A dermoscopic image of a skin lesion.
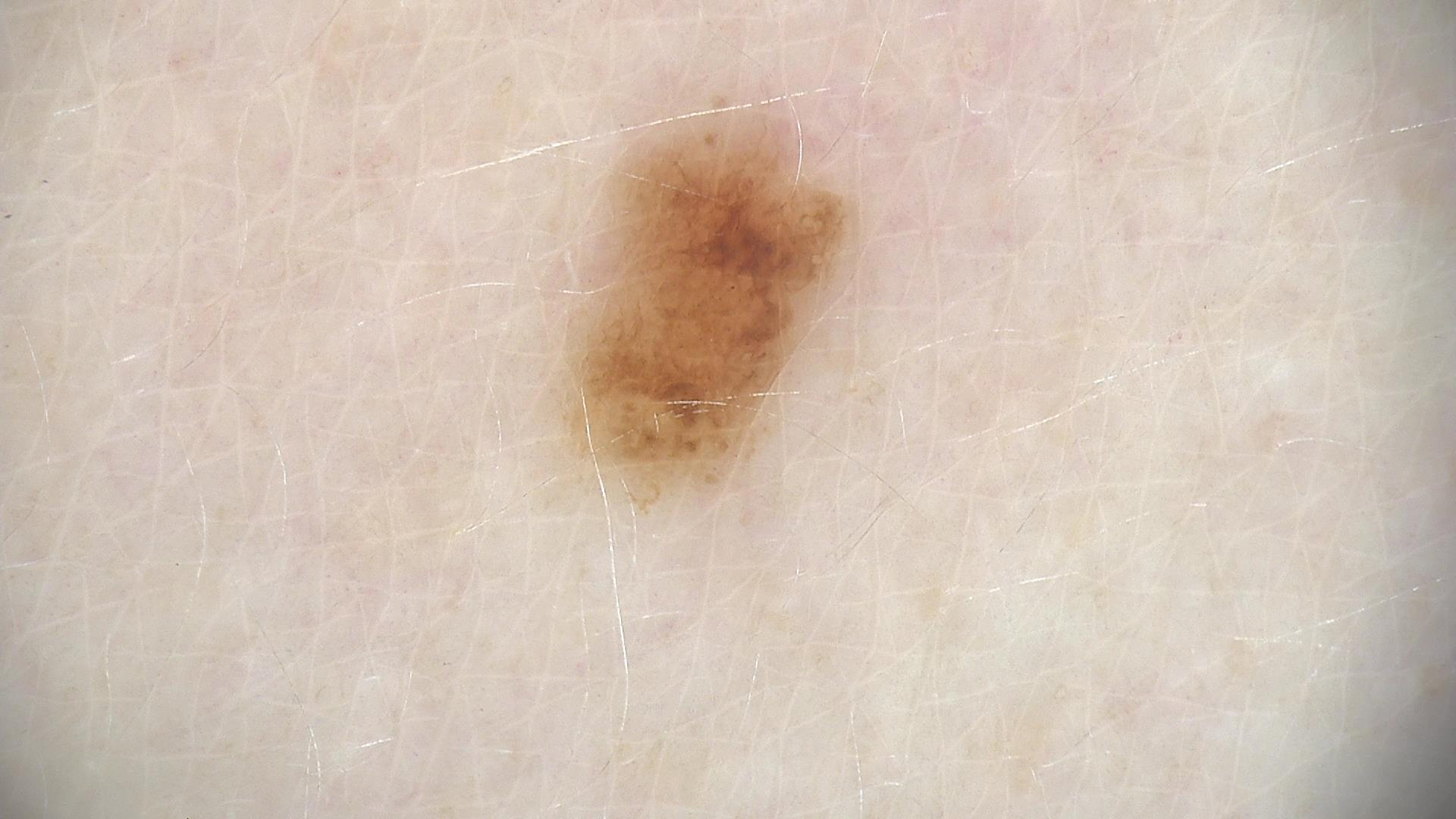Diagnosed as a dysplastic junctional nevus.